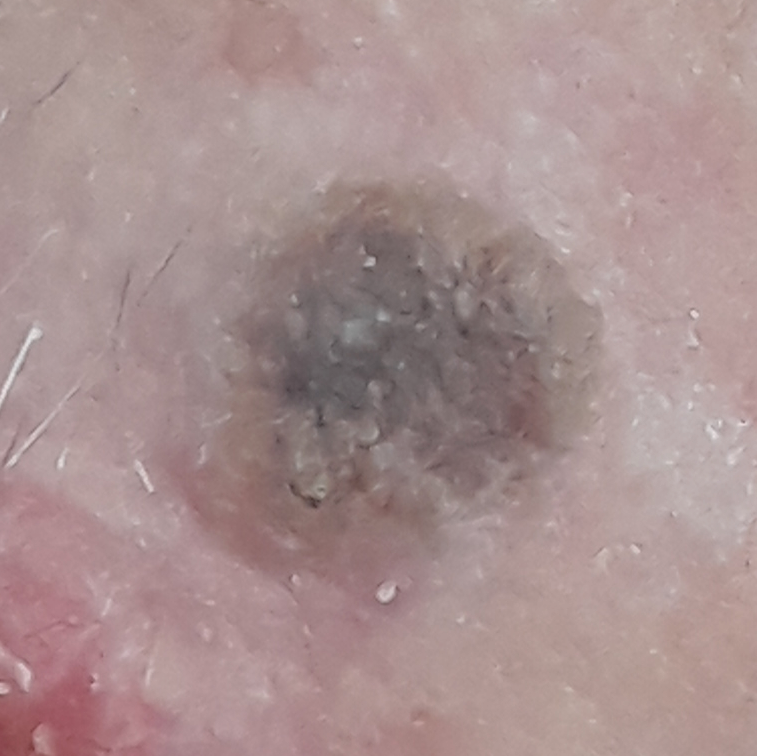Case:
– subject · male, age 79
– modality · clinical photo
– FST · II
– risk factors · no tobacco use, no alcohol use
– anatomic site · the face
– diameter · 14 × 14 mm
– reported symptoms · elevation / no change in appearance
– assessment · seborrheic keratosis (clinical consensus)